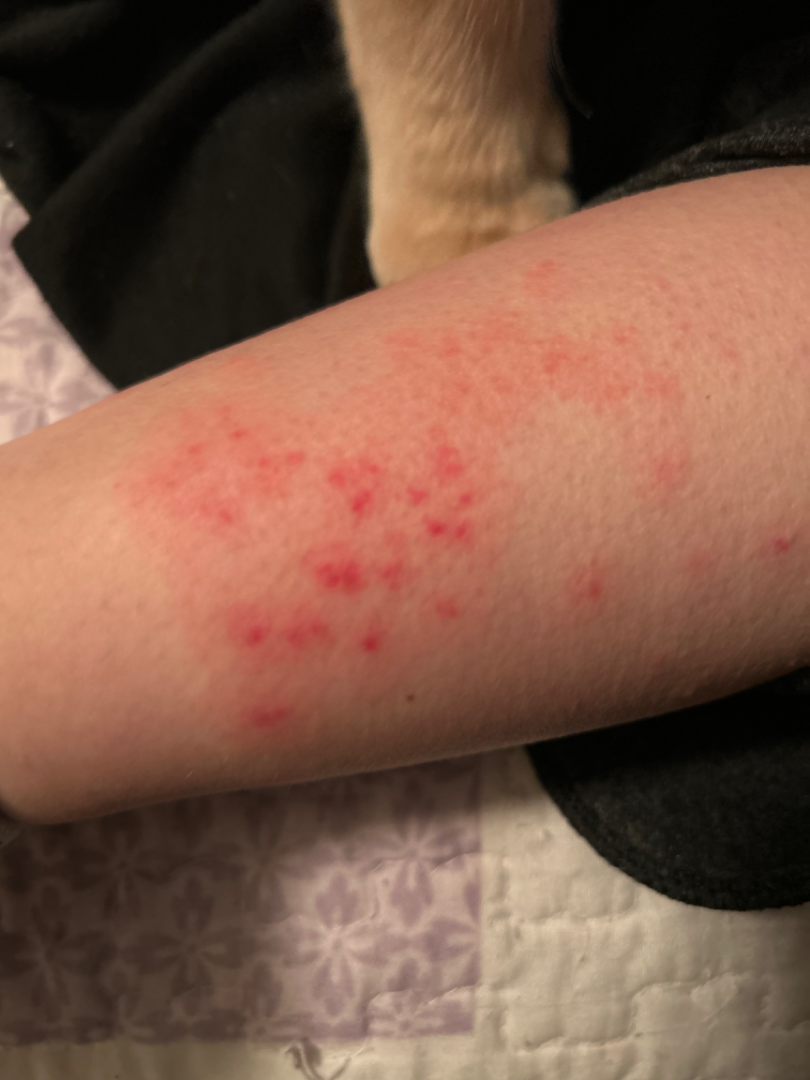Clinical context:
The contributor reports the lesion is flat. Symptoms reported: bothersome appearance. Self-categorized by the patient as a rash. The lesion involves the leg. This is a close-up image. The contributor reports the condition has been present for less than one week.
Assessment:
Folliculitis and Acute dermatitis, NOS were each considered, in no particular order.